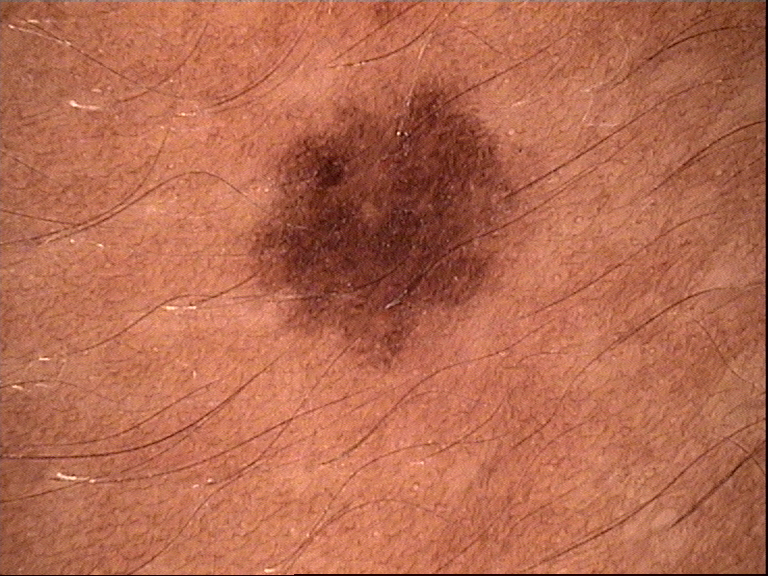image: dermatoscopy; label: dysplastic junctional nevus (expert consensus).